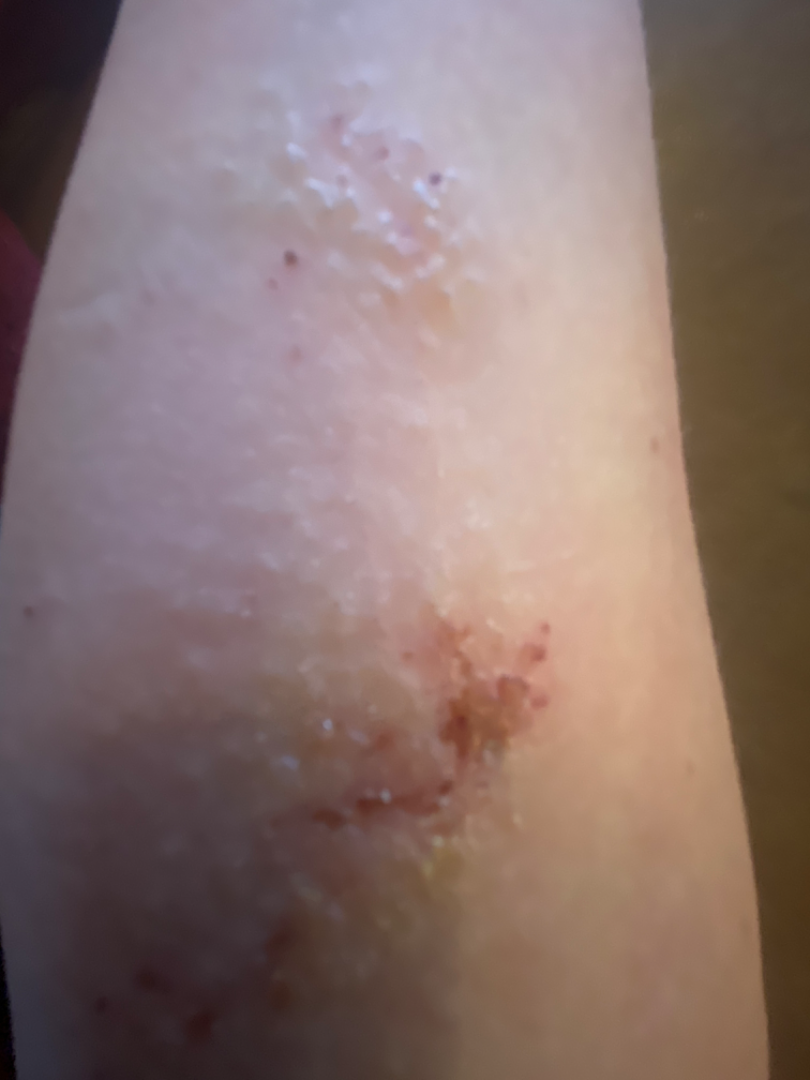Review: The reviewing dermatologist was unable to assign a differential diagnosis from the image. Patient information: Reported duration is one to four weeks. Located on the arm. The photograph is a close-up of the affected area. The patient indicates itching and burning. No associated systemic symptoms reported. The patient indicates the lesion is rough or flaky and raised or bumpy.